A dermoscopy image of a skin lesion; acquired for a research image collection, with no referral diagnosis; a male subject aged 62; few moles overall by the patient's own estimate:
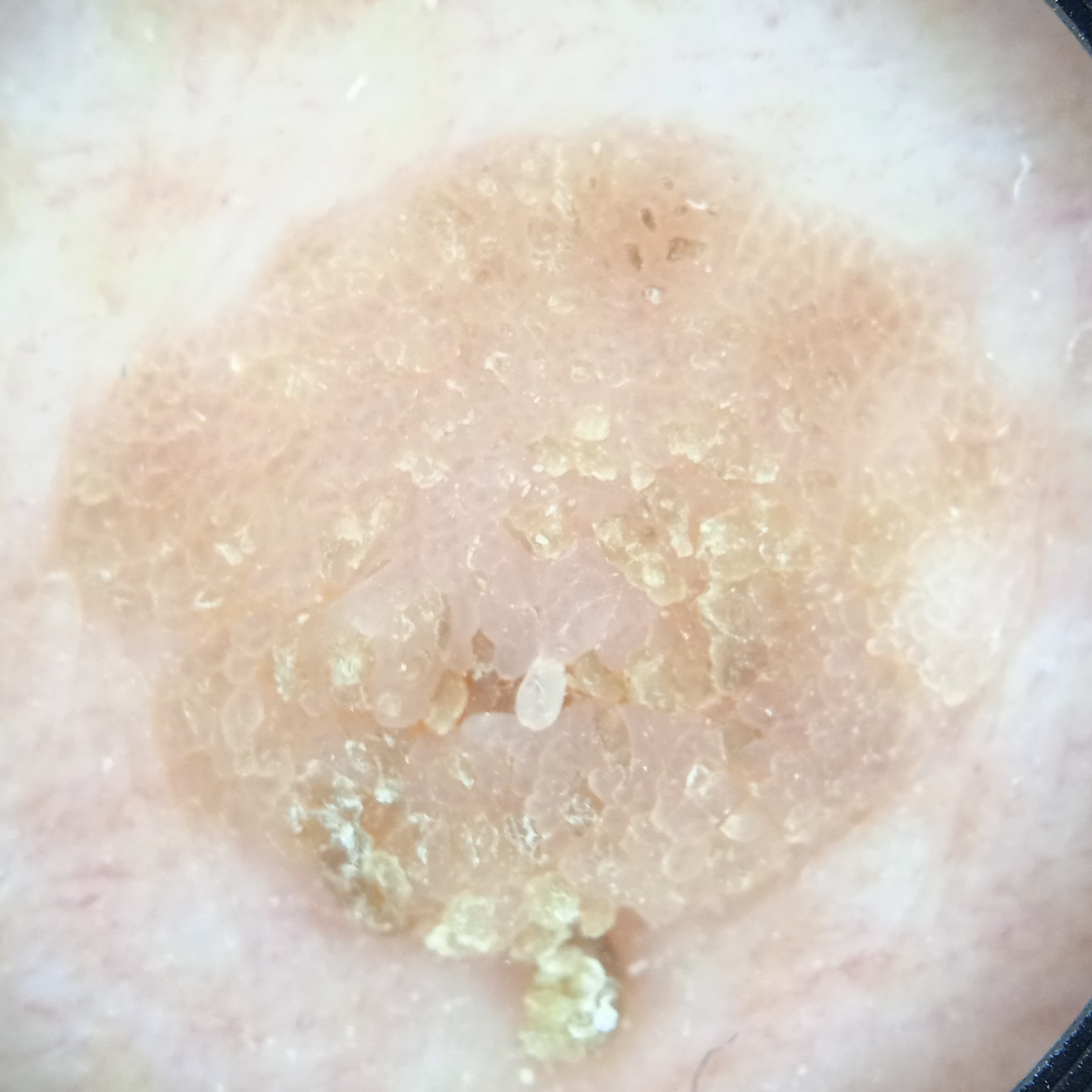anatomic site=the torso
diameter=11.3 mm
diagnosis=seborrheic keratosis (dermatologist consensus)